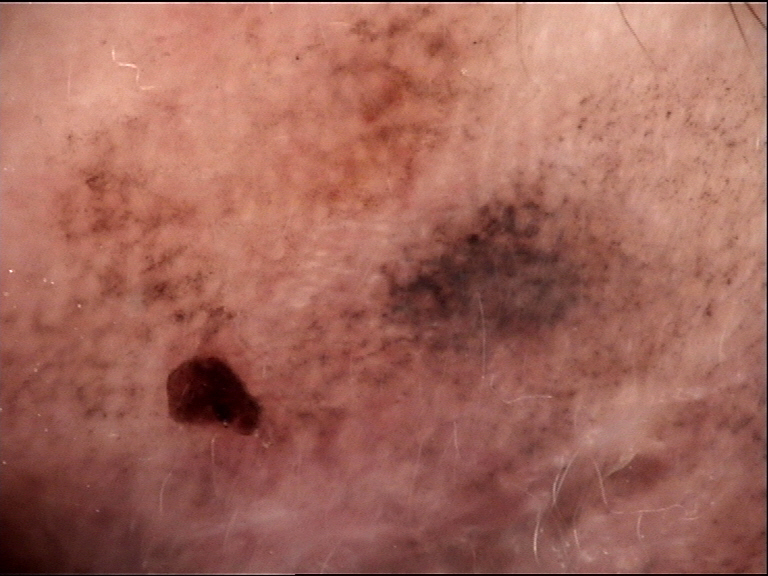A dermoscopic close-up of a skin lesion. Confirmed on histopathology as a lentigo maligna.